Texture is reported as fluid-filled and raised or bumpy · Fitzpatrick phototype V · the patient described the issue as a rash · the lesion is associated with bothersome appearance, itching, pain and burning · the condition has been present for one to four weeks · the photo was captured at an angle · the lesion involves the head or neck: 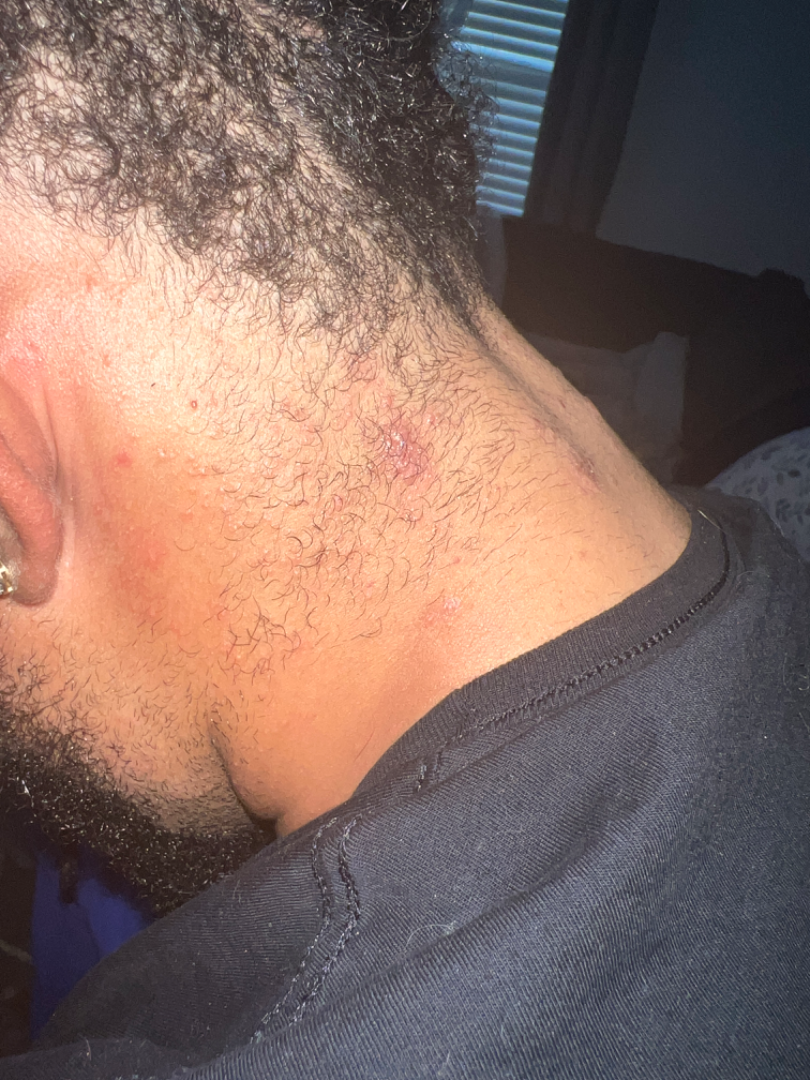Q: Could the case be diagnosed?
A: indeterminate